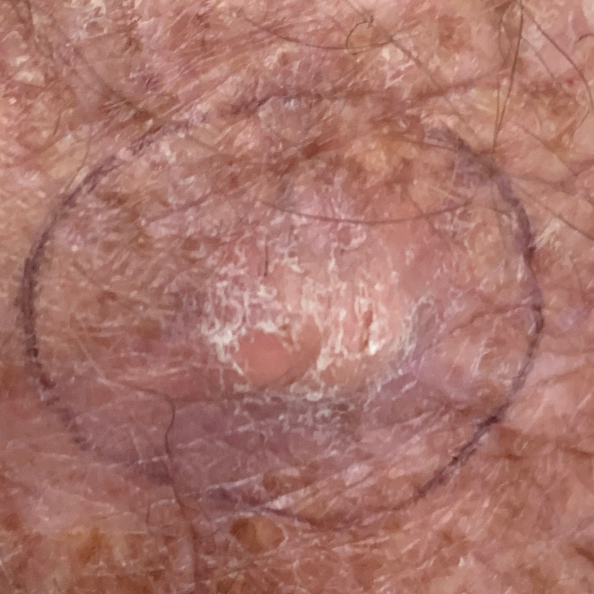exposure history: pesticide exposure, prior malignancy (patient or family), prior skin cancer (patient or family), no tobacco use; anatomic site: a forearm; patient-reported symptoms: elevation, itching / no bleeding; pathology: squamous cell carcinoma (biopsy-proven).